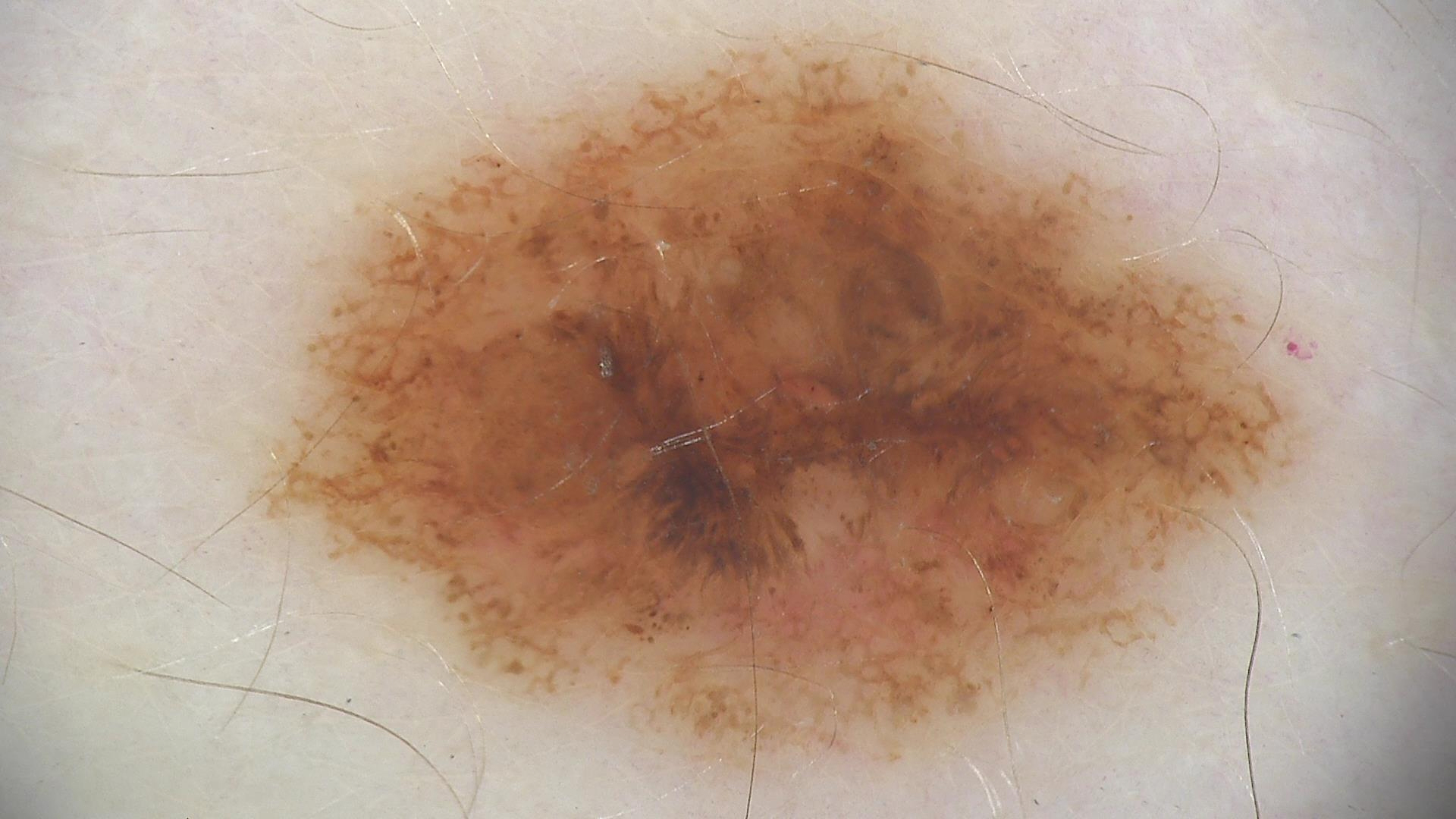Findings:
- imaging: dermatoscopy
- pathology: melanoma (biopsy-proven)